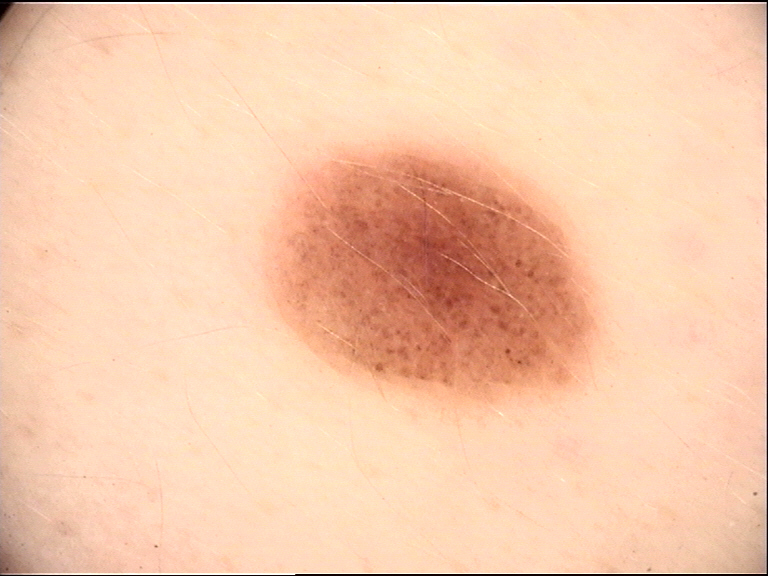label: dysplastic compound nevus (expert consensus).